A dermoscopic photograph of a skin lesion.
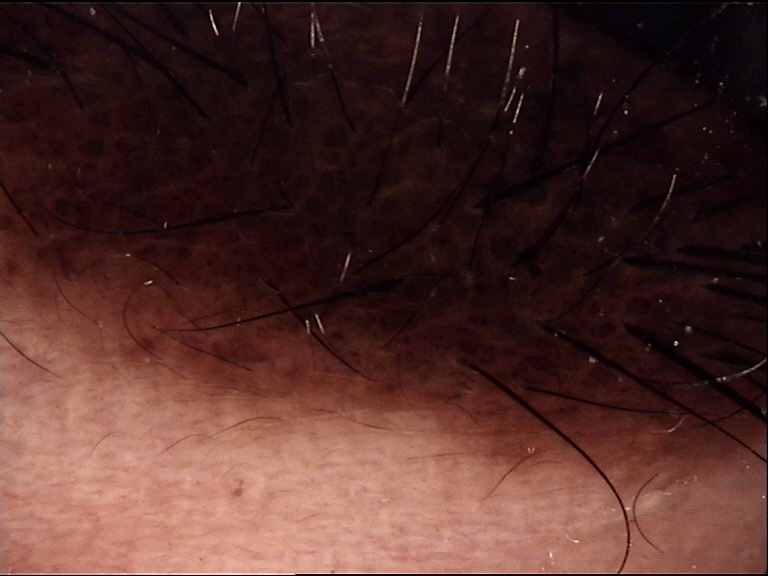• category — banal
• label — congenital compound nevus (expert consensus)